Dermoscopy of a skin lesion: 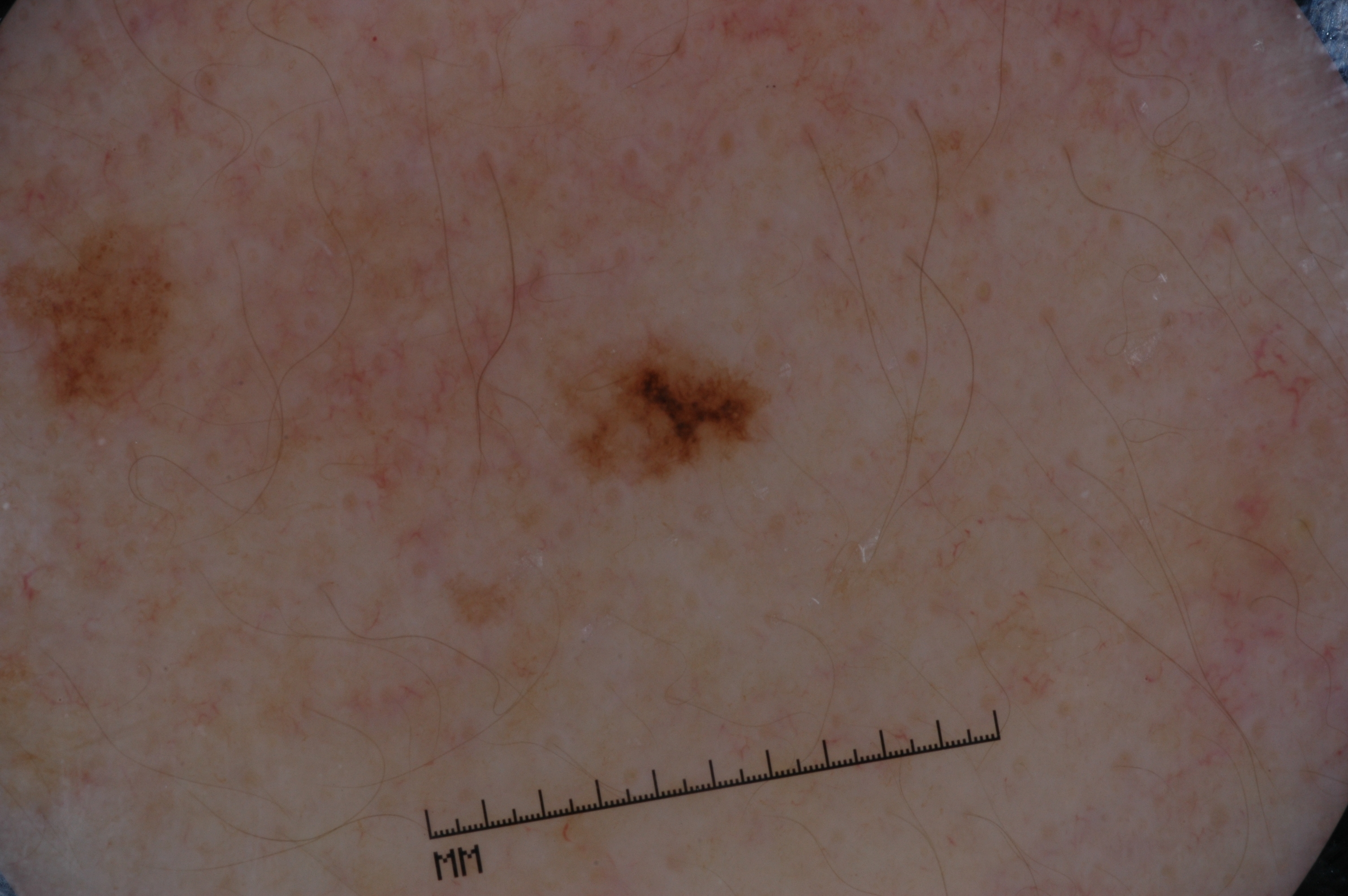Dermoscopic review identifies no pigment network, streaks, negative network, or milia-like cysts. The lesion is small relative to the field of view. In (x1, y1, x2, y2) order, the lesion spans 579, 343, 758, 476. The diagnostic assessment was a melanocytic nevus, a benign lesion.